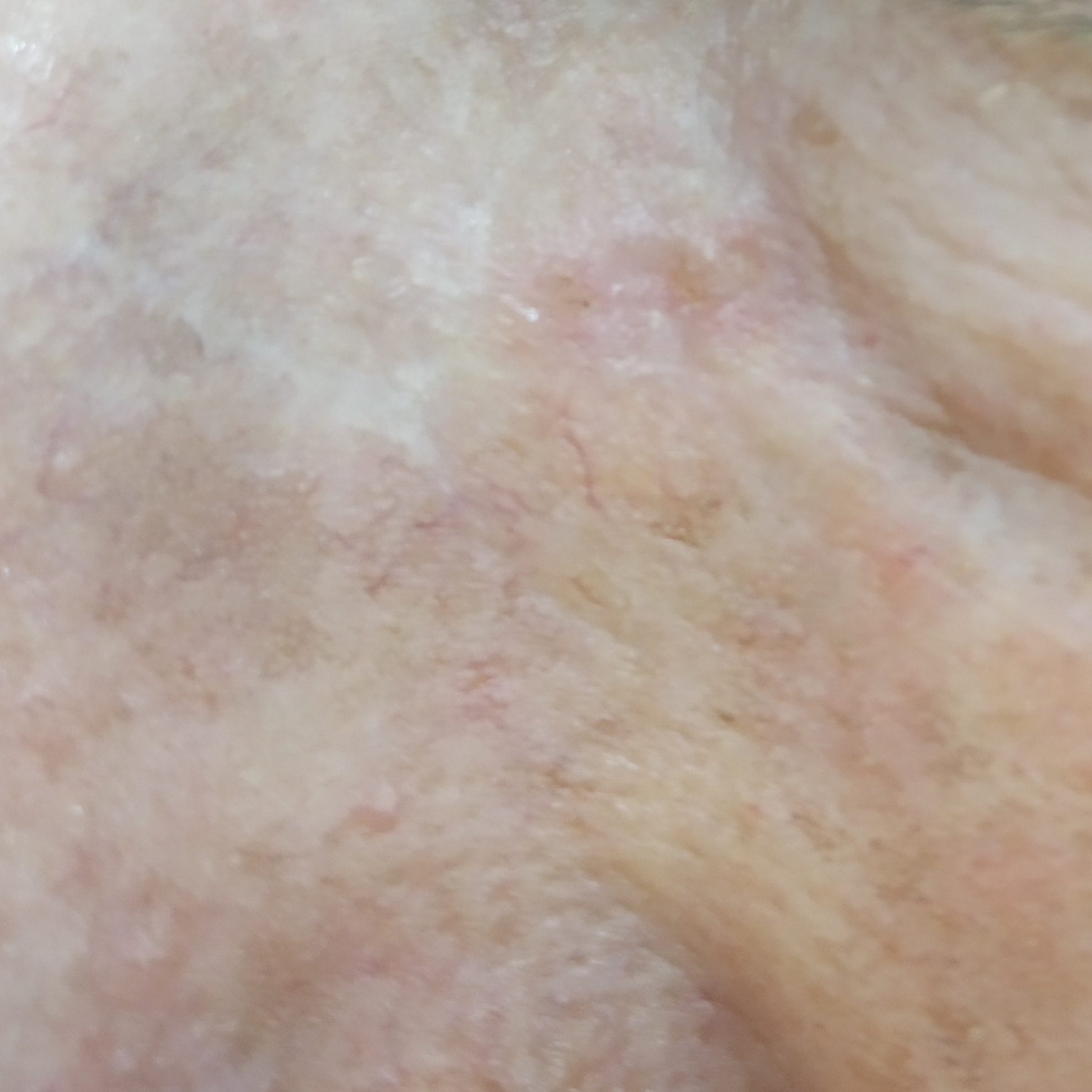exposures: pesticide exposure, alcohol use, prior skin cancer (patient or family), prior malignancy (patient or family)
patient: male, aged 59
skin phototype: IV
modality: smartphone clinical photo
location: the face
lesion size: 4 × 3 mm
symptoms: no pain, no itching
diagnostic label: basal cell carcinoma (biopsy-proven)